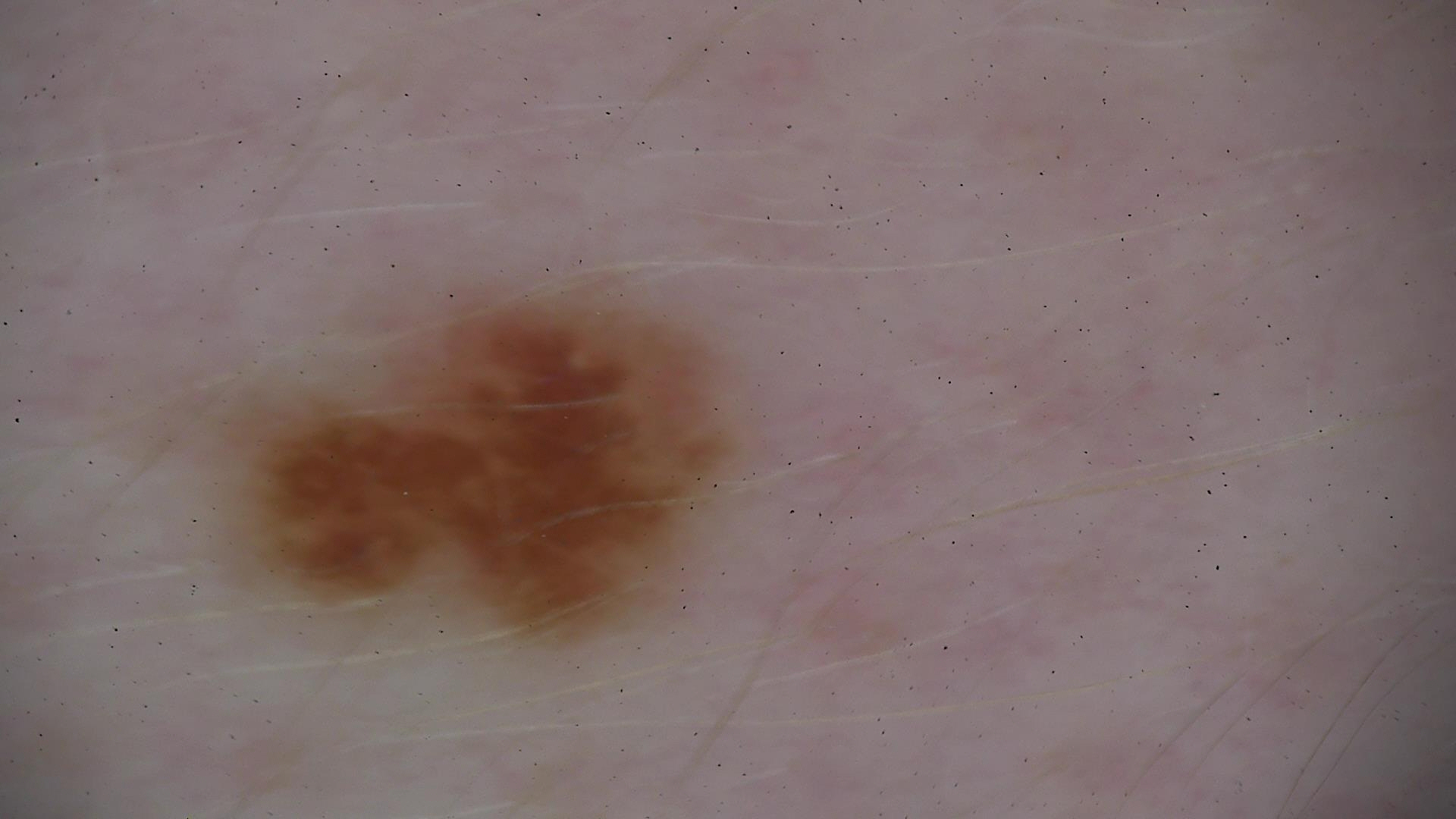Findings:
A dermoscopic photograph of a skin lesion.
Conclusion:
The diagnosis was a dysplastic junctional nevus.